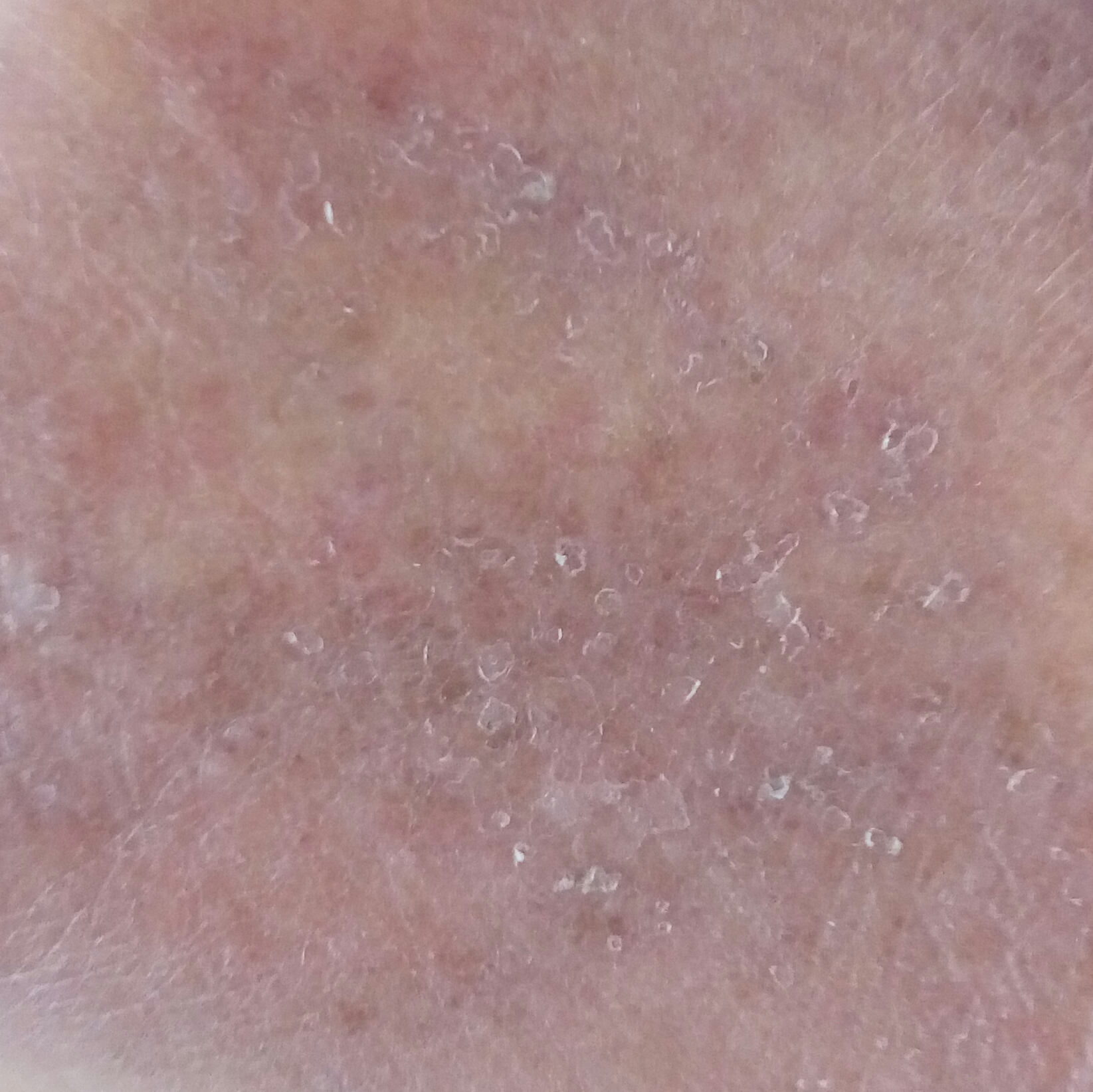Clinical context:
A clinical close-up photograph of a skin lesion. A subject aged 57. The lesion involves a hand.
Conclusion:
Consistent with an actinic keratosis.